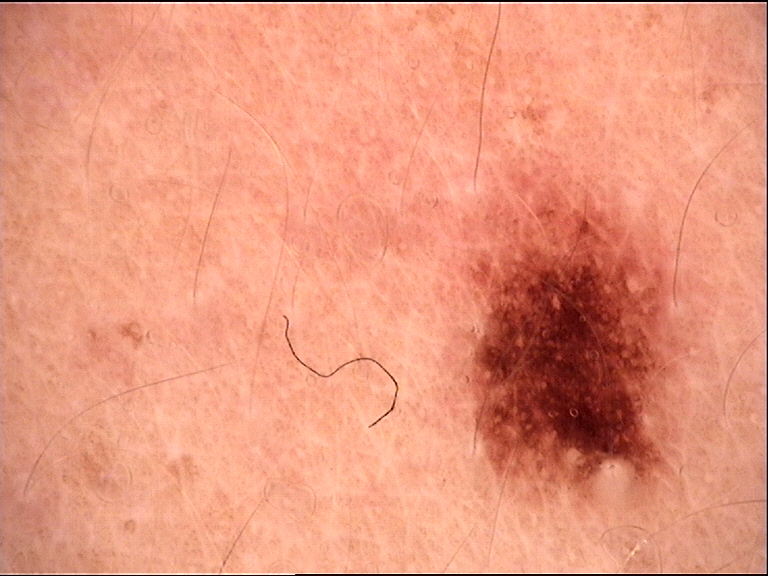Summary:
The morphology is that of a banal lesion.
Impression:
The diagnosis was a junctional nevus.